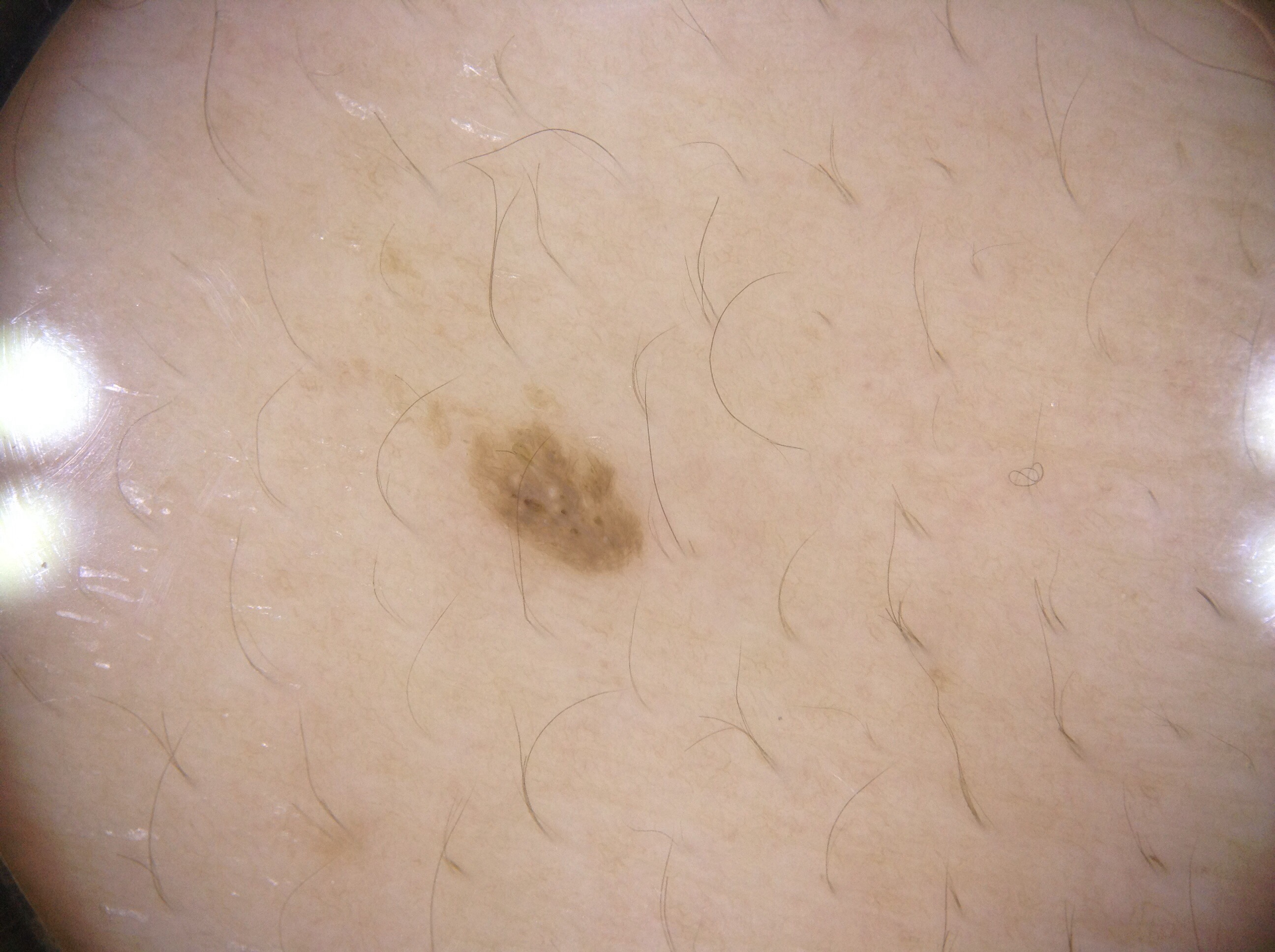A dermoscopic image of a skin lesion.
A female subject roughly 65 years of age.
A small lesion within a wider field of skin.
The lesion occupies the region x1=488 y1=432 x2=638 y2=565.
The dermoscopic pattern shows milia-like cysts.
Consistent with a seborrheic keratosis, a keratinocytic lesion.